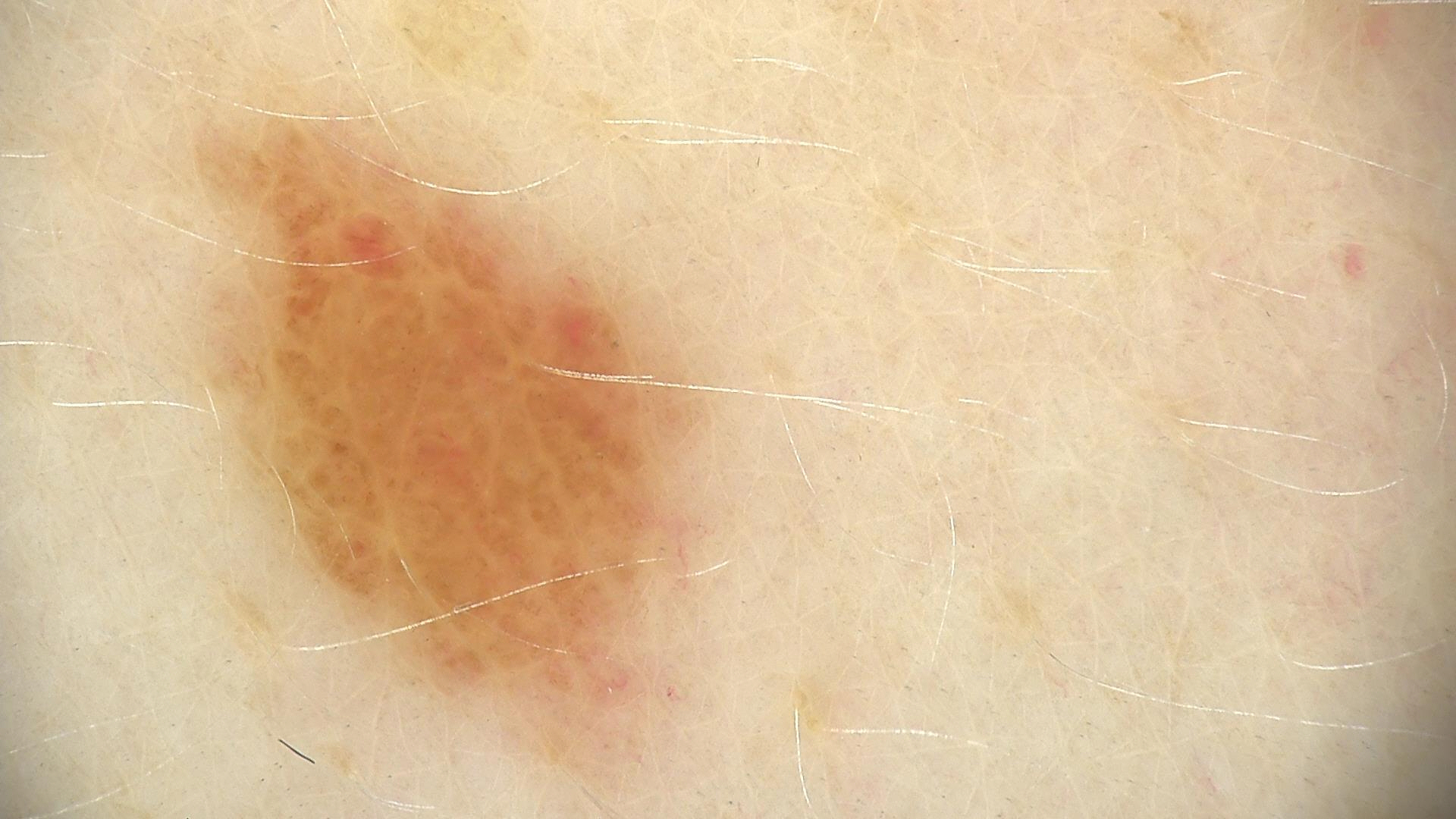A dermoscopic photograph of a skin lesion.
Classified as a banal lesion — a junctional nevus.